A dermoscopy image of a single skin lesion.
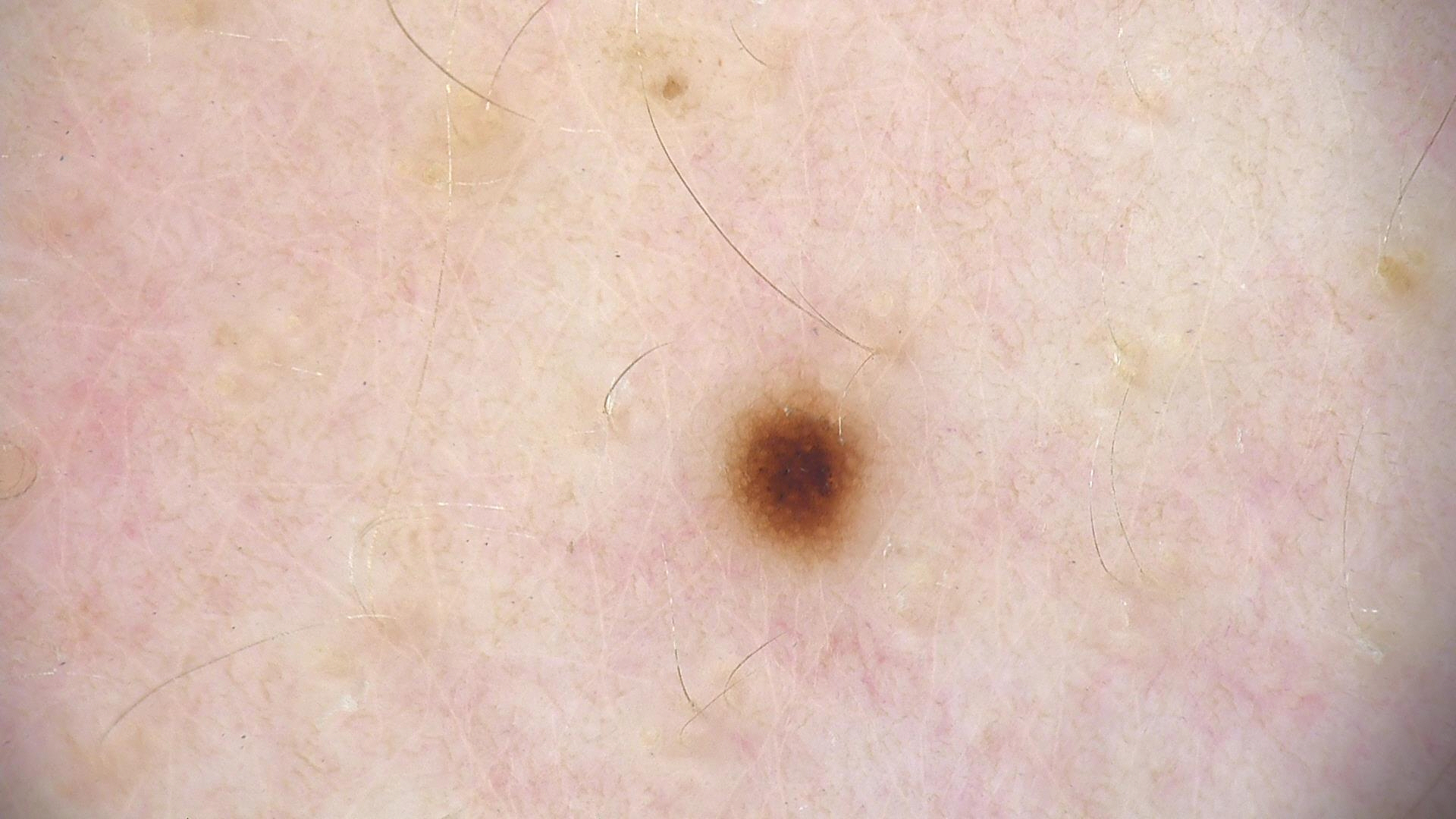Q: What is the diagnosis?
A: dysplastic junctional nevus (expert consensus)